A male patient, aged 48-52. A skin lesion imaged with a dermatoscope:
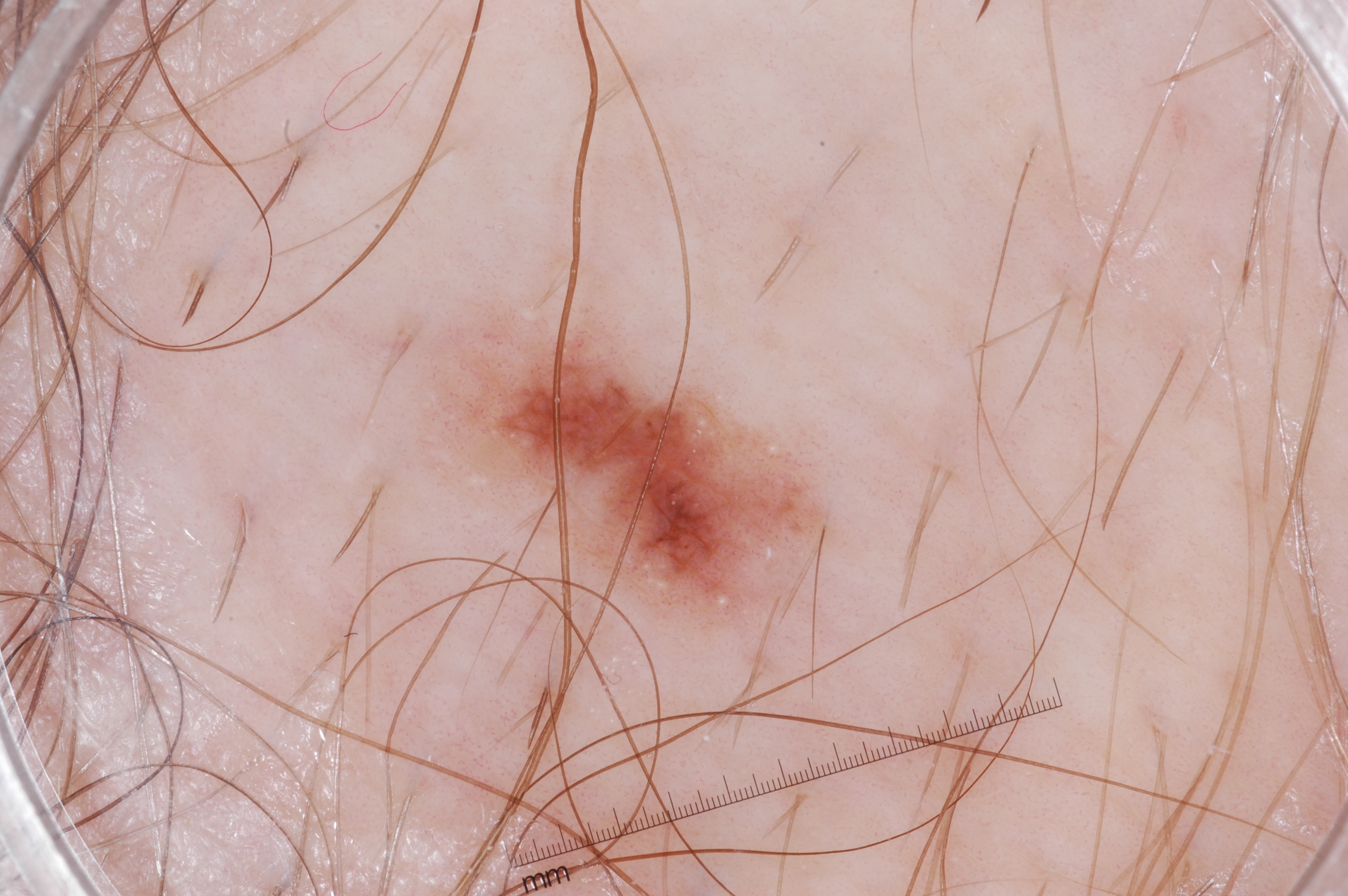  dermoscopic_features:
    present:
      - milia-like cysts
      - pigment network
    absent:
      - streaks
      - negative network
  lesion_extent:
    approx_field_fraction_pct: 5
  lesion_location:
    bbox_xyxy:
      - 453
      - 315
      - 822
      - 602
  diagnosis:
    name: melanocytic nevus
    malignancy: benign
    lineage: melanocytic
    provenance: clinical